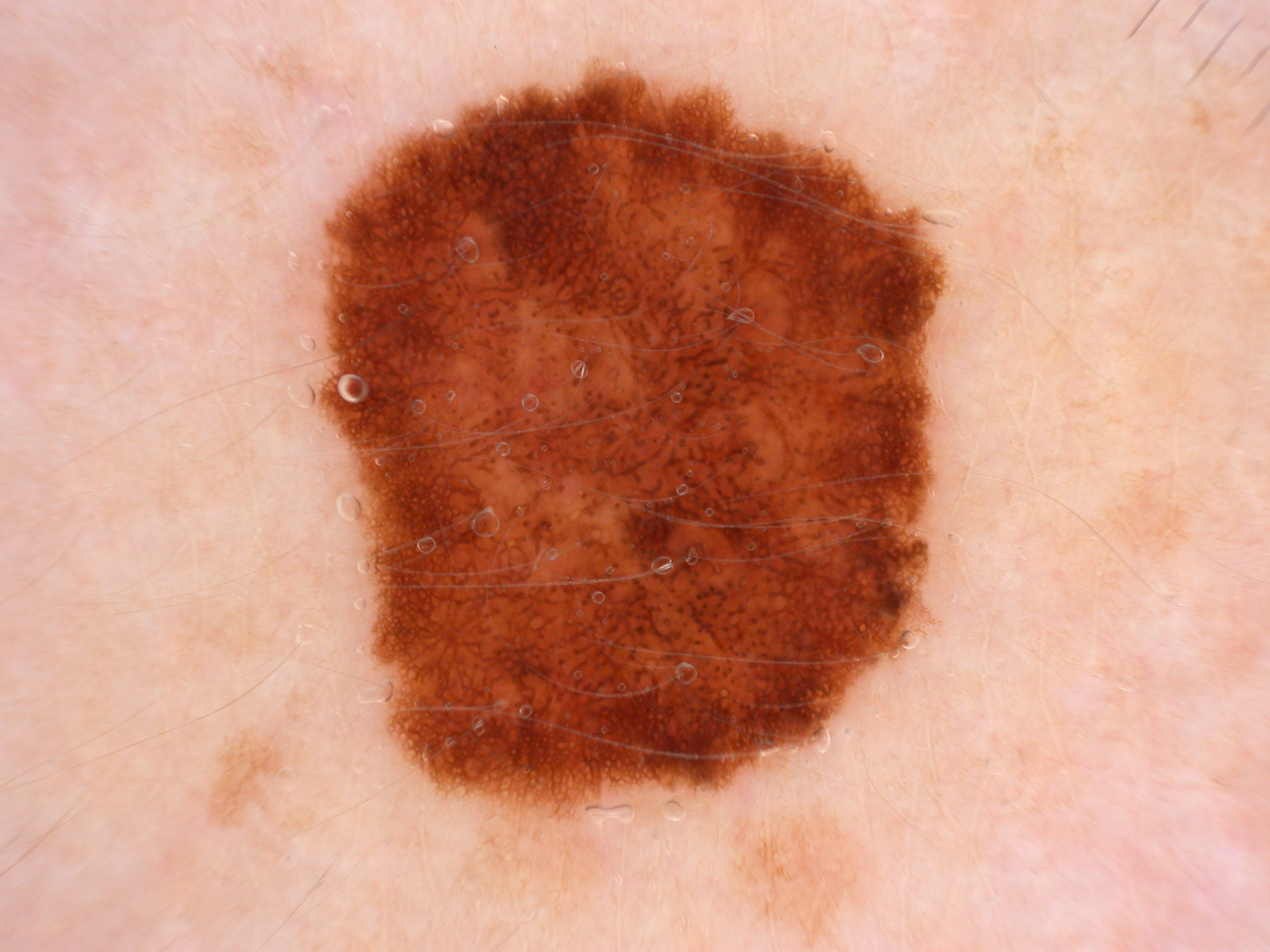Image and clinical context: A dermoscopic view of a skin lesion. The visible lesion spans 311, 68, 946, 815. Dermoscopic assessment notes globules and pigment network. Diagnosis: Histopathology confirmed a melanoma.